The photograph is a close-up of the affected area.
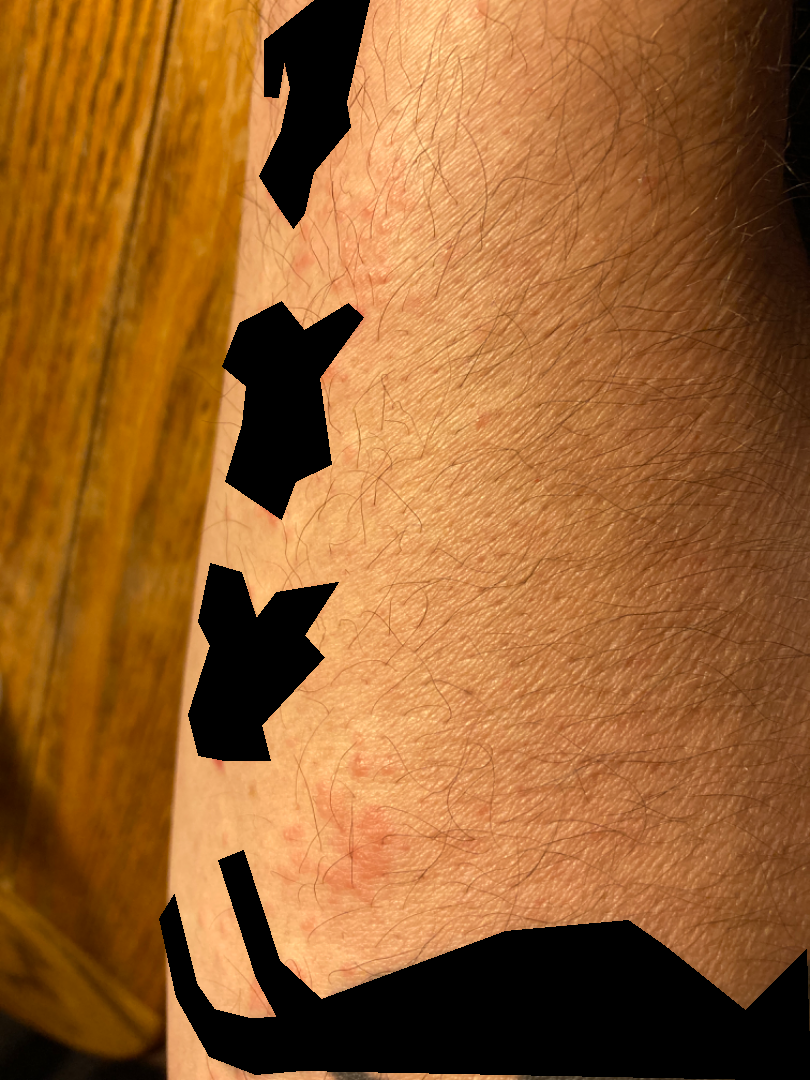On dermatologist assessment of the image, the differential, in no particular order, includes Eczema and Allergic Contact Dermatitis.